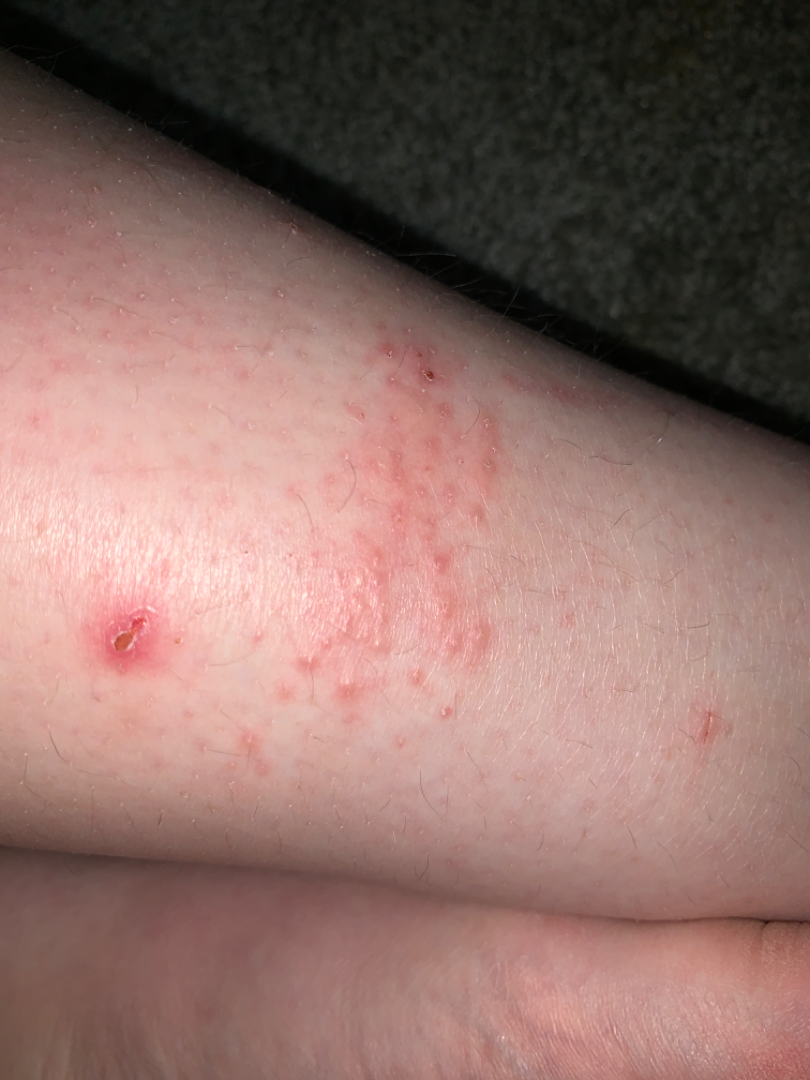Impression: The reviewer was unable to grade this case for skin condition. History: Female patient, age 18–29. The lesion involves the leg. The patient considered this a rash. The lesion is described as raised or bumpy. Symptoms reported: bleeding and itching. Close-up view.